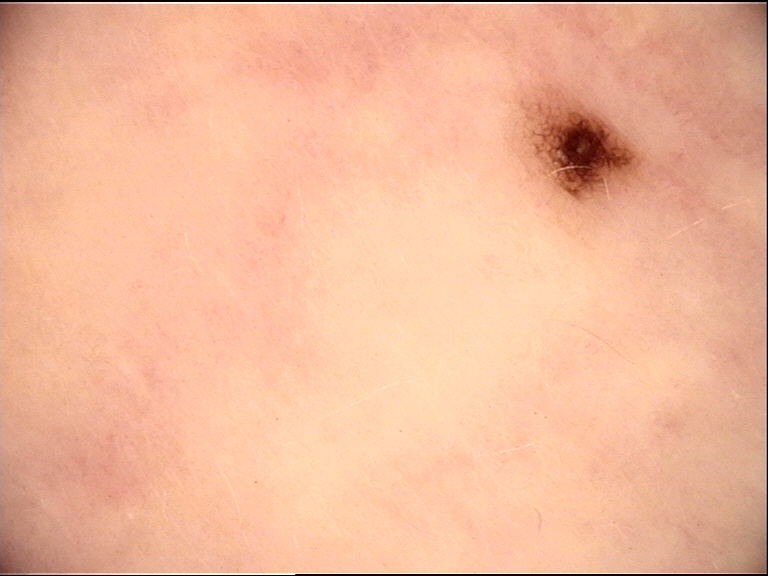The diagnostic label was a junctional nevus.